A skin lesion imaged with a dermatoscope.
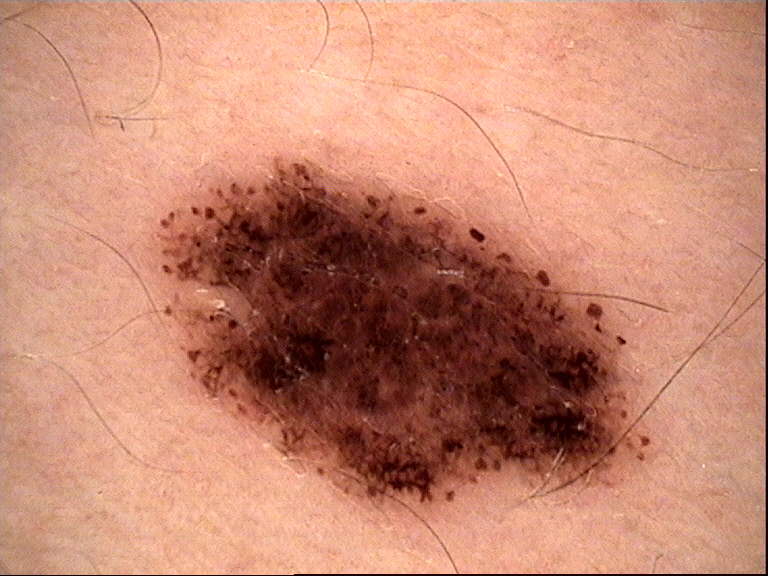Q: What is the diagnosis?
A: dysplastic compound nevus (expert consensus)